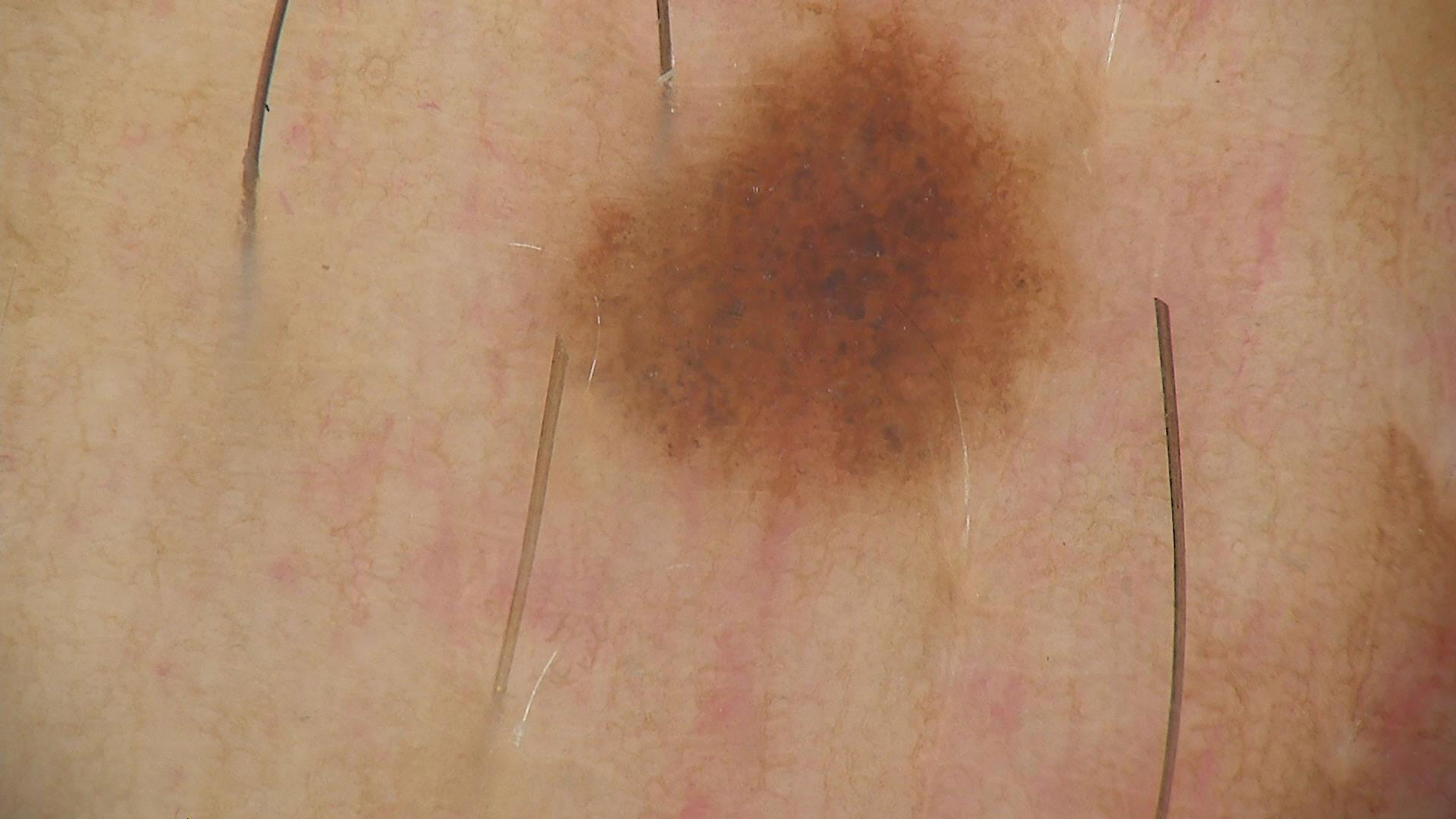Case: A skin lesion imaged with a dermatoscope. Conclusion: The diagnostic label was a dysplastic junctional nevus.